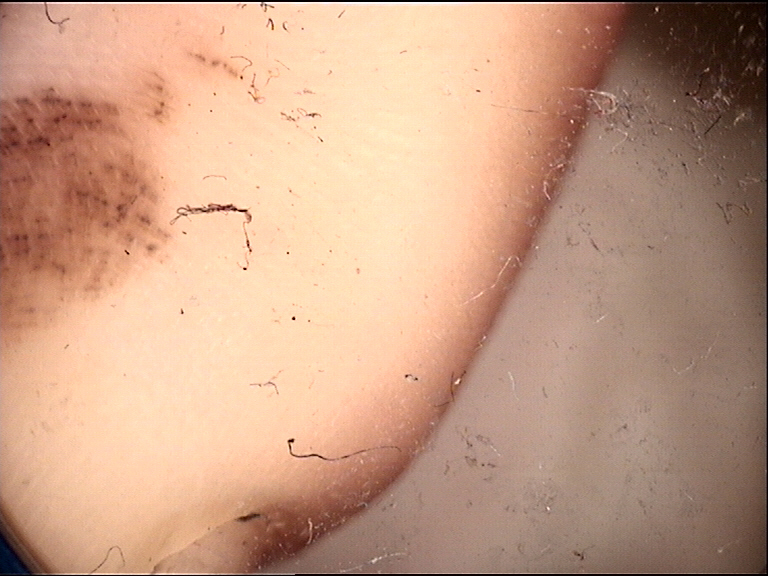| key | value |
|---|---|
| image type | dermatoscopy |
| class | acral junctional nevus (expert consensus) |